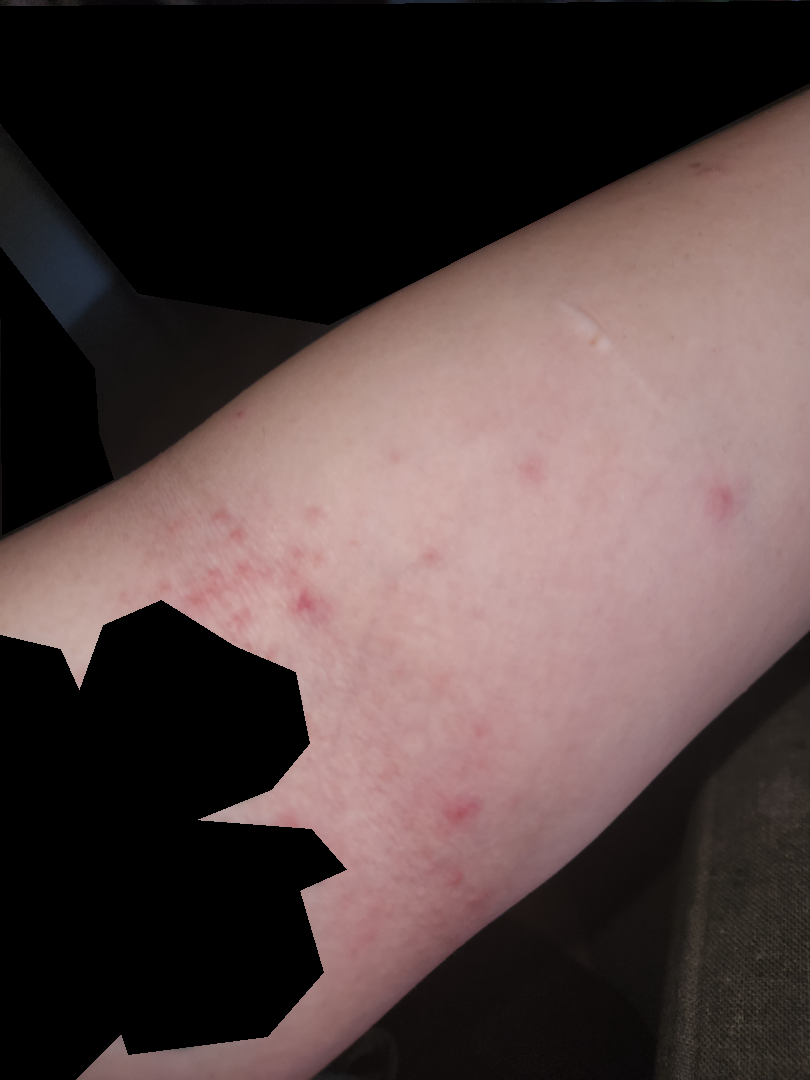Eczema (most likely).